A male patient aged around 65 · a skin lesion imaged with contact-polarized dermoscopy: 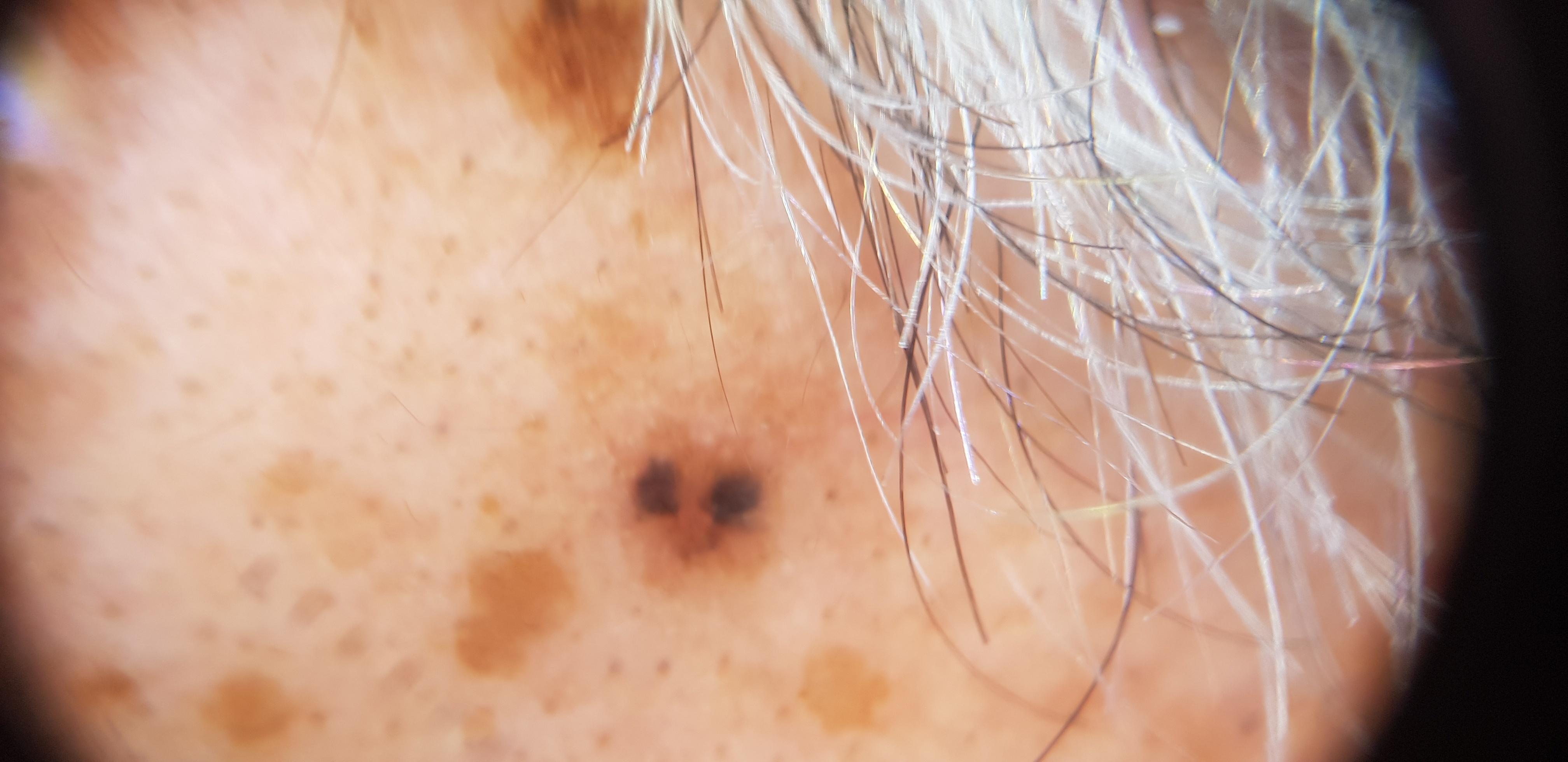Clinical context: The lesion is located on the head or neck. Conclusion: On biopsy, the diagnosis was a basal cell carcinoma.